A dermoscopy image of a single skin lesion:
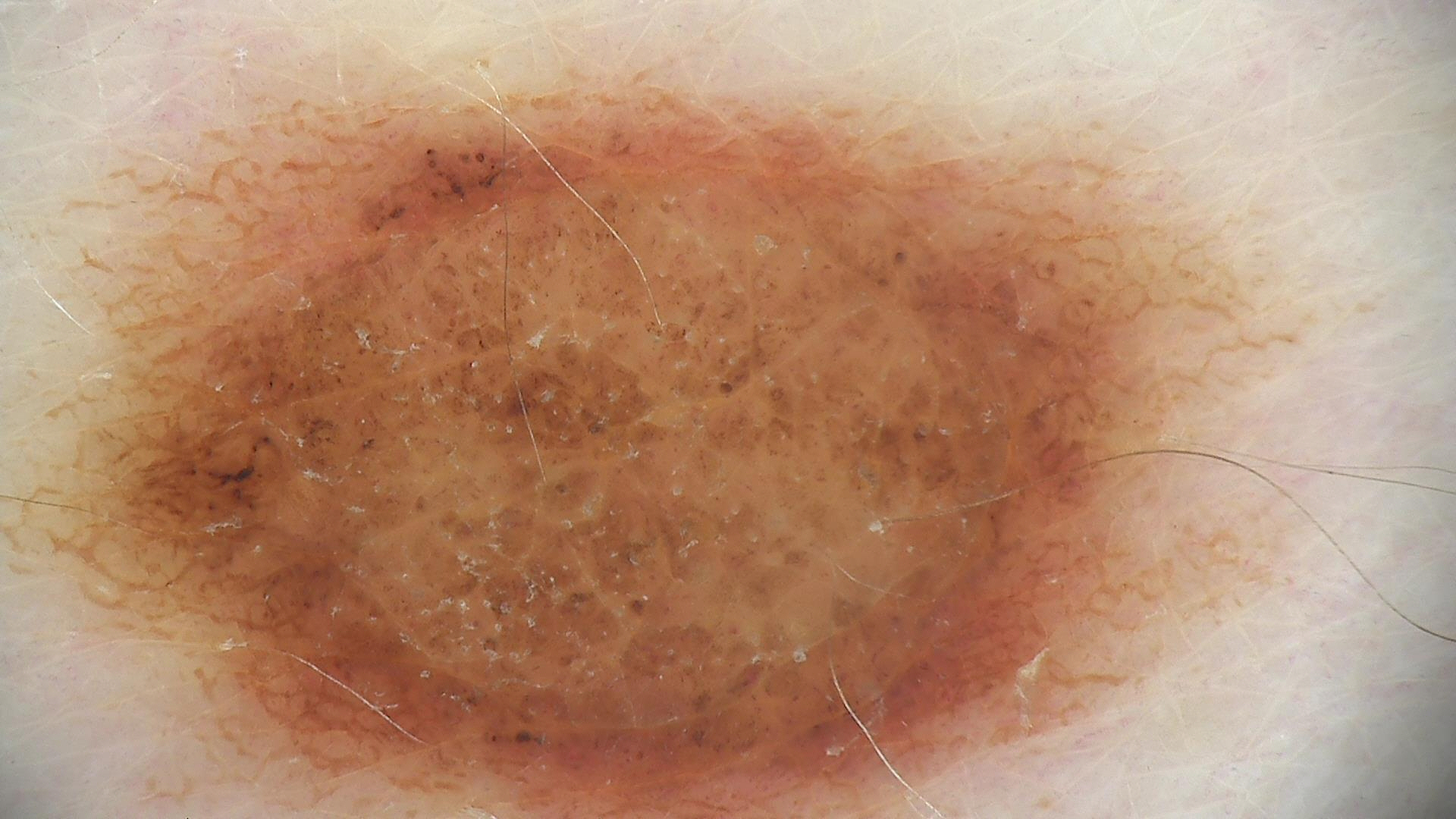The diagnostic label was a dysplastic compound nevus.